The chart records a previous melanoma · a female patient in their 60s · a skin lesion imaged with contact-polarized dermoscopy — 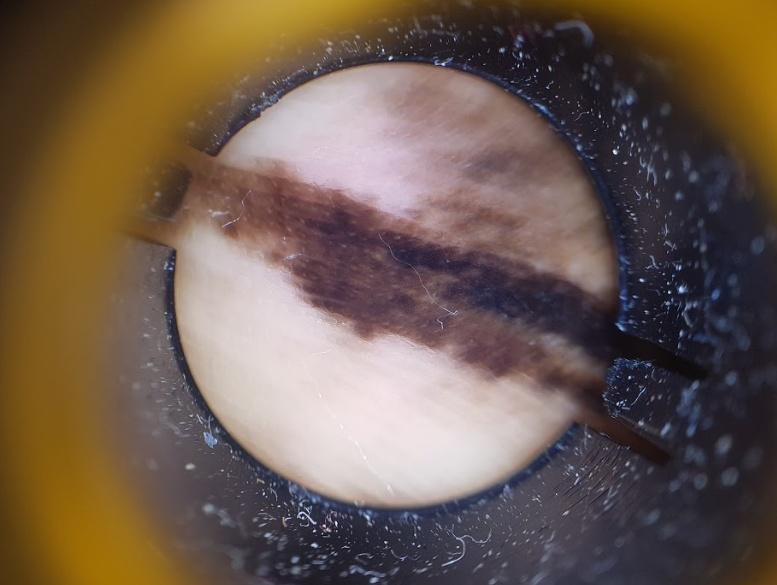| key | value |
|---|---|
| anatomic site | an acral site (palms or soles) |
| diagnosis | Melanoma (biopsy-proven) |